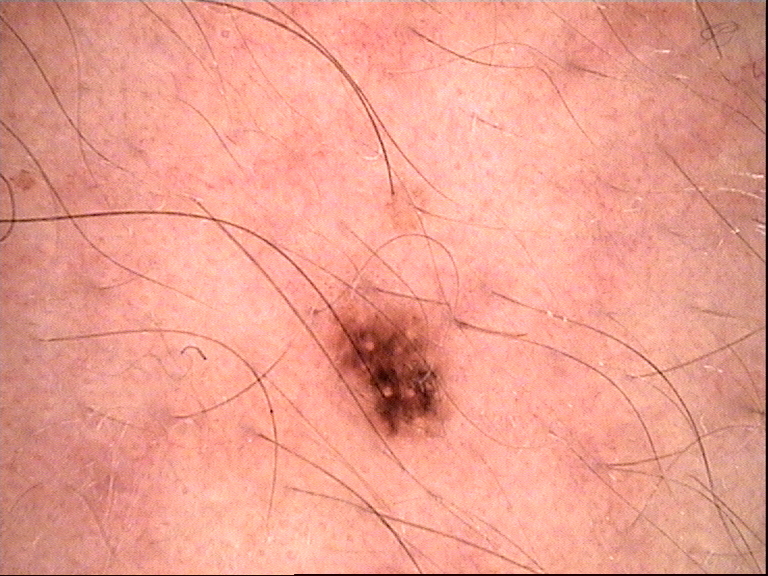<case>
<image>dermoscopy</image>
<lesion_type>
<main_class>banal</main_class>
<pattern>compound</pattern>
</lesion_type>
<diagnosis>
<name>Miescher nevus</name>
<code>mcb</code>
<malignancy>benign</malignancy>
<super_class>melanocytic</super_class>
<confirmation>expert consensus</confirmation>
</diagnosis>
</case>